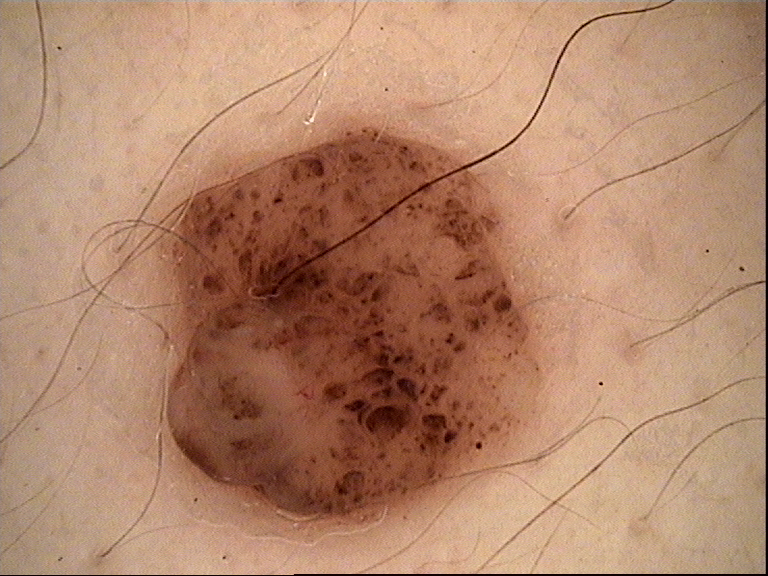The diagnosis was a dermal nevus.